A dermoscopic close-up of a skin lesion:
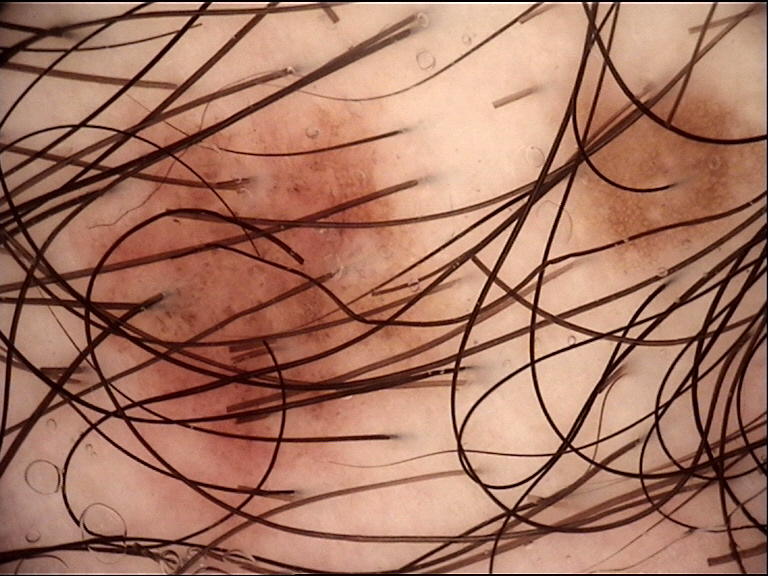Findings:
– assessment · dysplastic junctional nevus (expert consensus)